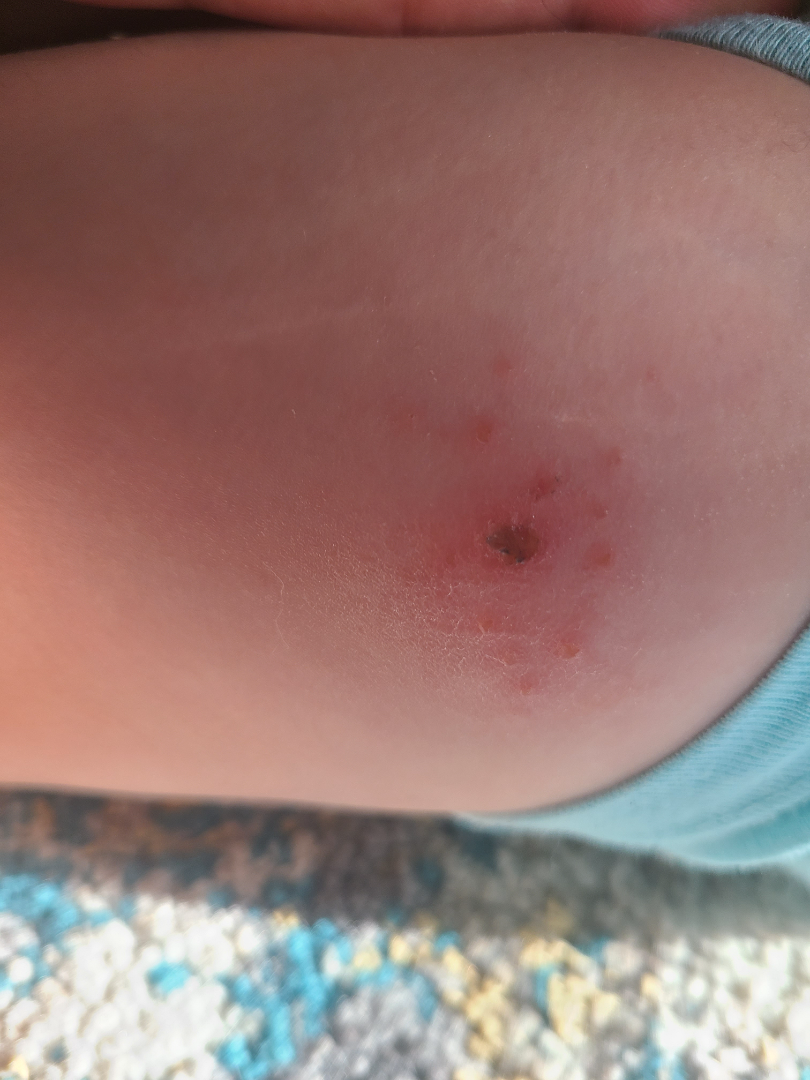assessment = indeterminate from the photograph
systemic symptoms = none reported
present for = less than one week
patient's own categorization = a rash
framing = close-up
location = leg
patient-reported symptoms = enlargement, itching, burning, pain and bothersome appearance